A dermoscopic image of a skin lesion:
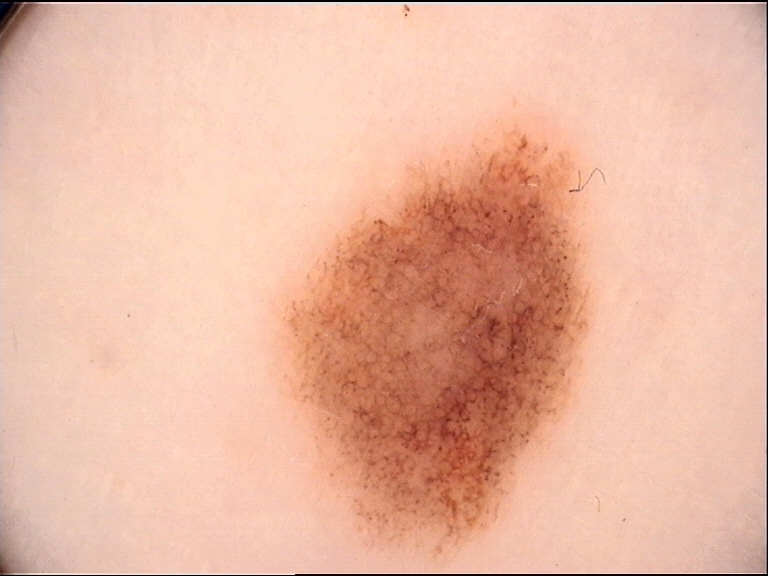The diagnosis was a dysplastic junctional nevus.